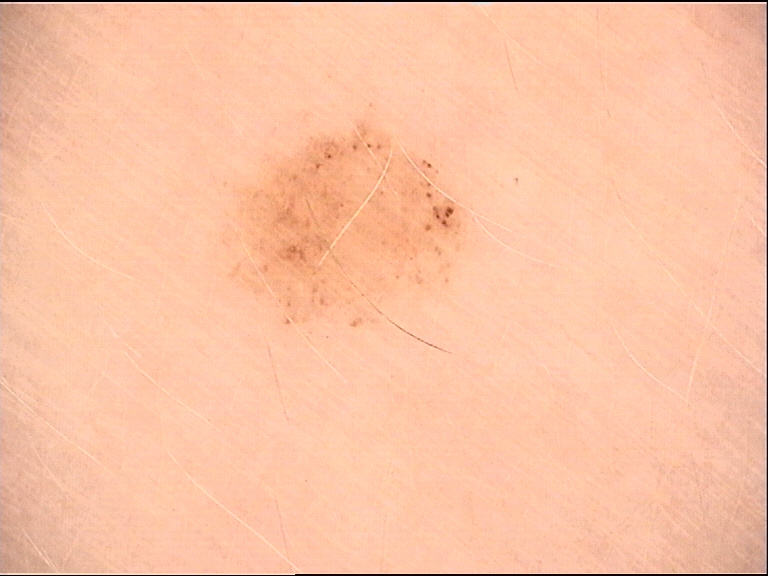Case:
A skin lesion imaged with a dermatoscope.
Impression:
Labeled as a benign lesion — a dysplastic junctional nevus.